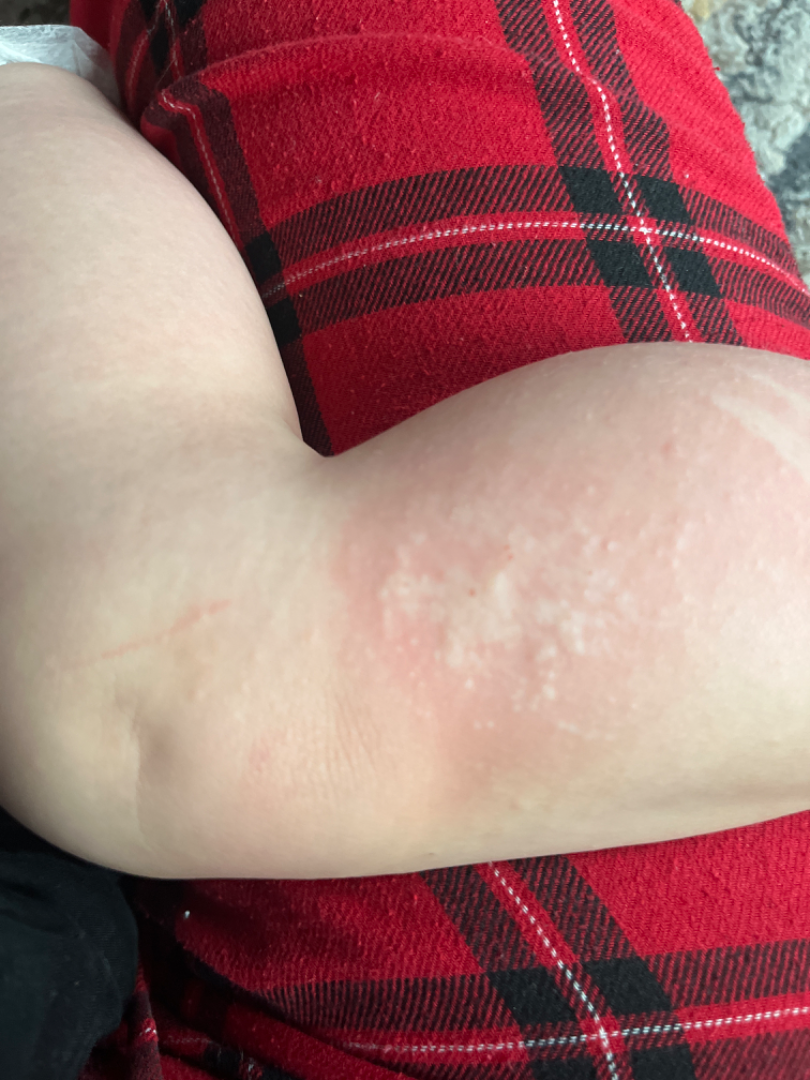<case>
<assessment>indeterminate</assessment>
<shot_type>close-up</shot_type>
<body_site>leg</body_site>
</case>